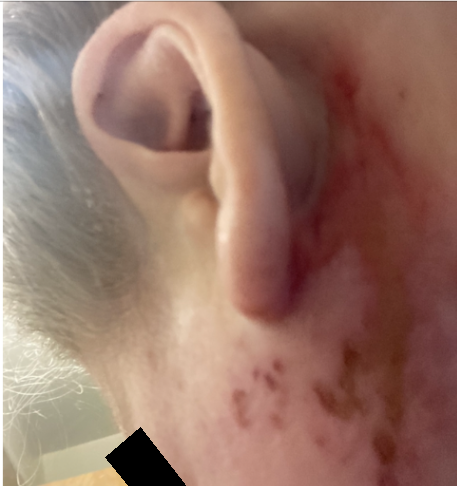| field | value |
|---|---|
| assessment | not assessable |
| framing | at an angle |